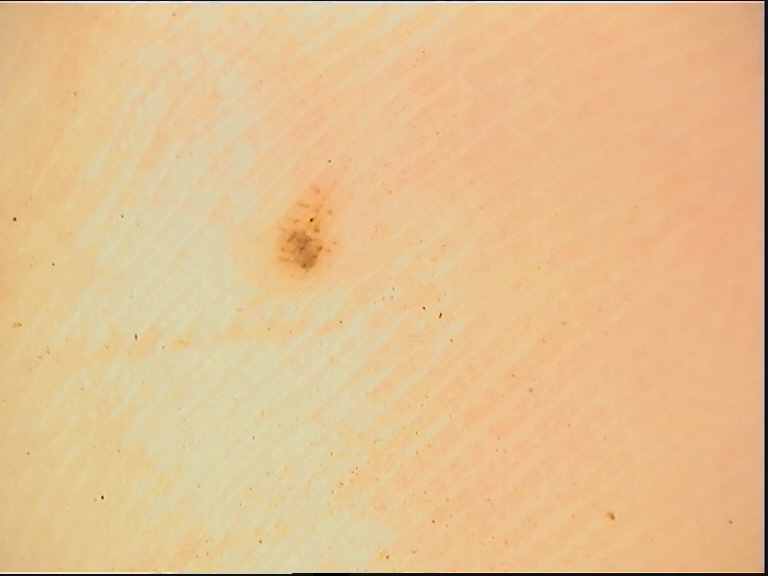Diagnosed as an acral dysplastic junctional nevus.